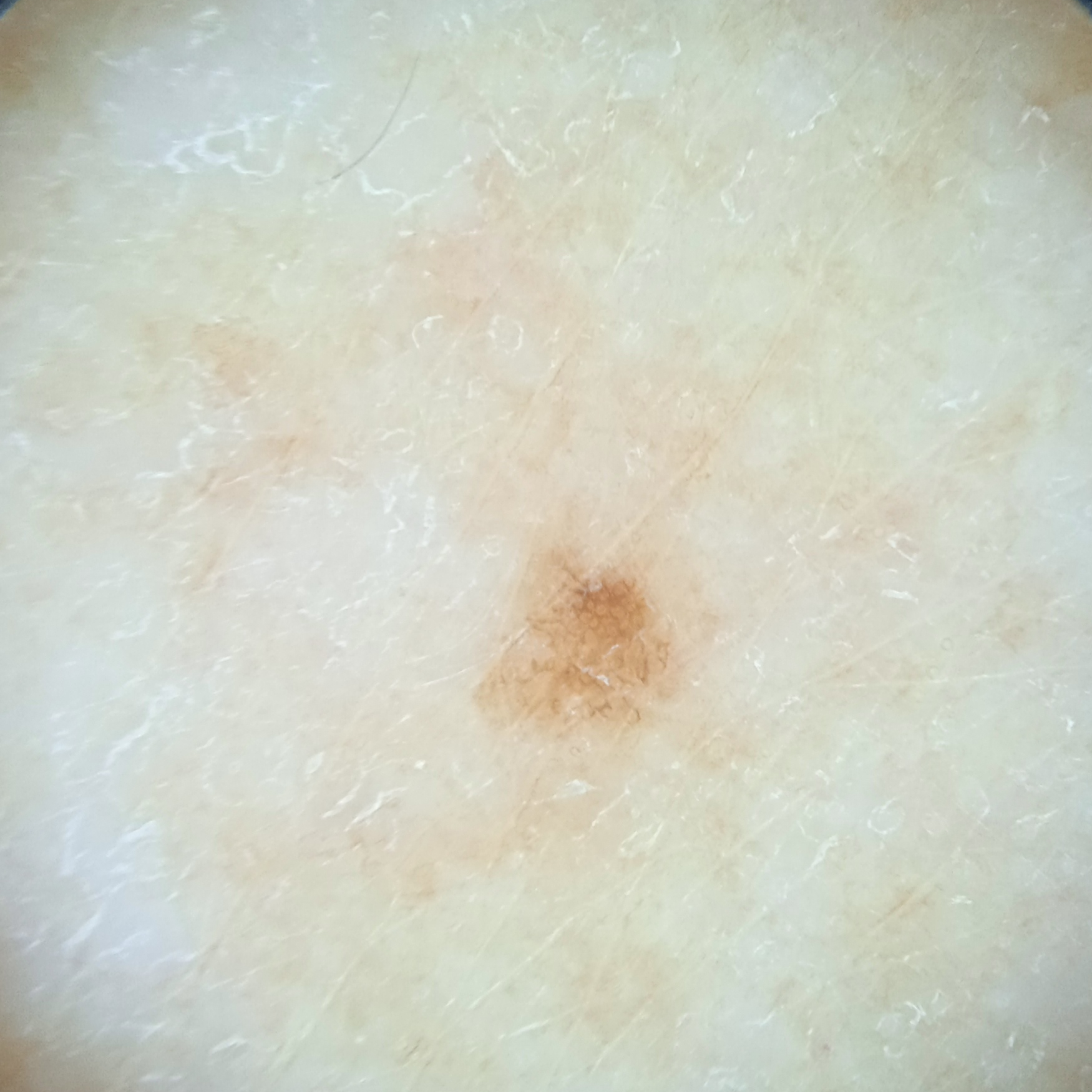Q: What was the diagnosis?
A: melanocytic nevus (dermatologist consensus)